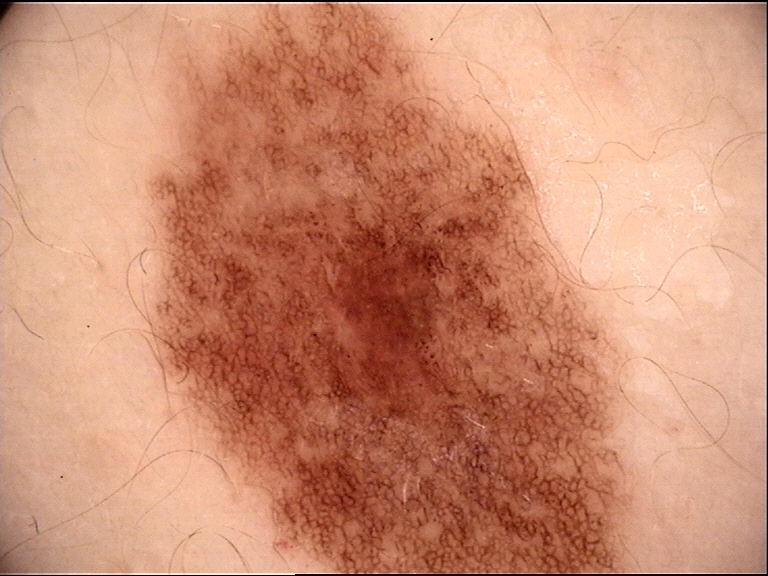A dermoscopic image of a skin lesion. The diagnosis was a benign lesion — a dysplastic junctional nevus.